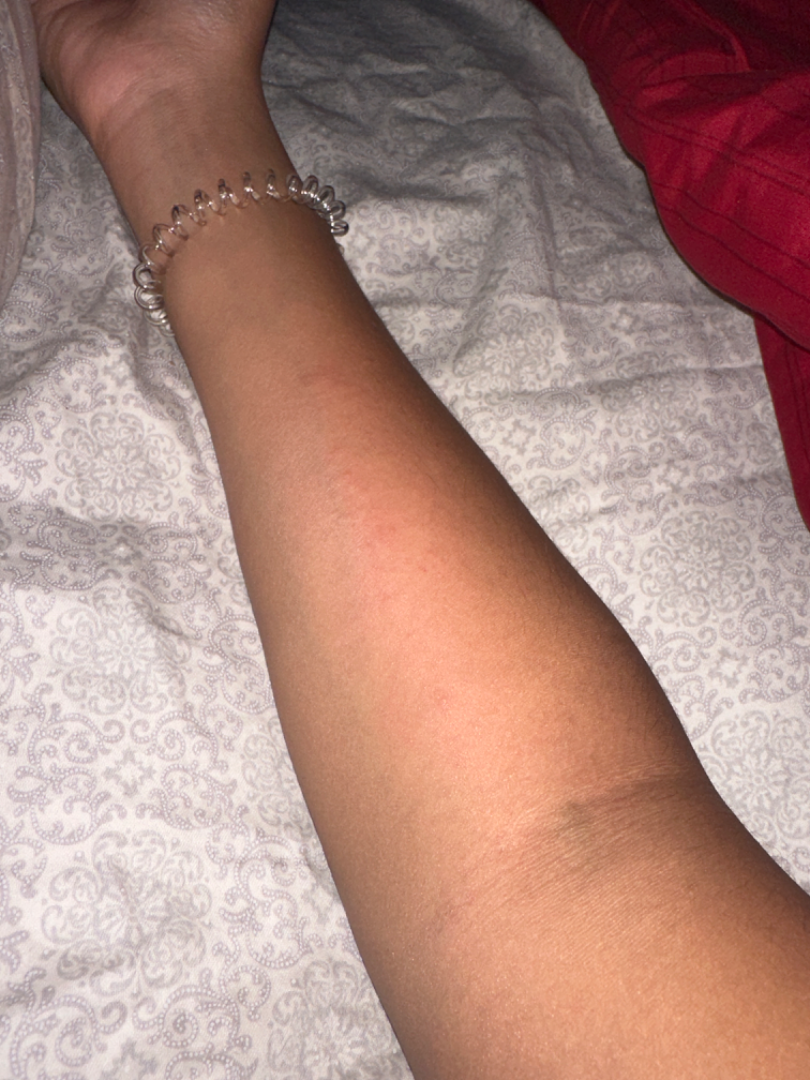Background: Skin tone: FST IV; human graders estimated Monk Skin Tone 4 or 5 (two reviewer pools). The patient notes the condition has been present for less than one week. The patient notes the lesion is raised or bumpy. A close-up photograph. Female subject, age 18–29. The affected area is the arm. Findings: The reviewing dermatologist's impression was: the differential, in no particular order, includes Hypersensitivity and Allergic Contact Dermatitis.